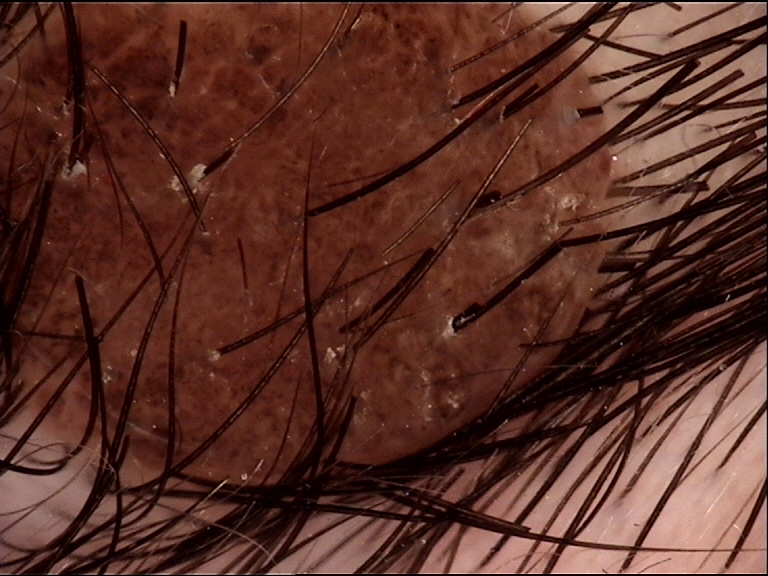diagnosis: dermal nevus (expert consensus).